A dermoscopic image of a skin lesion: 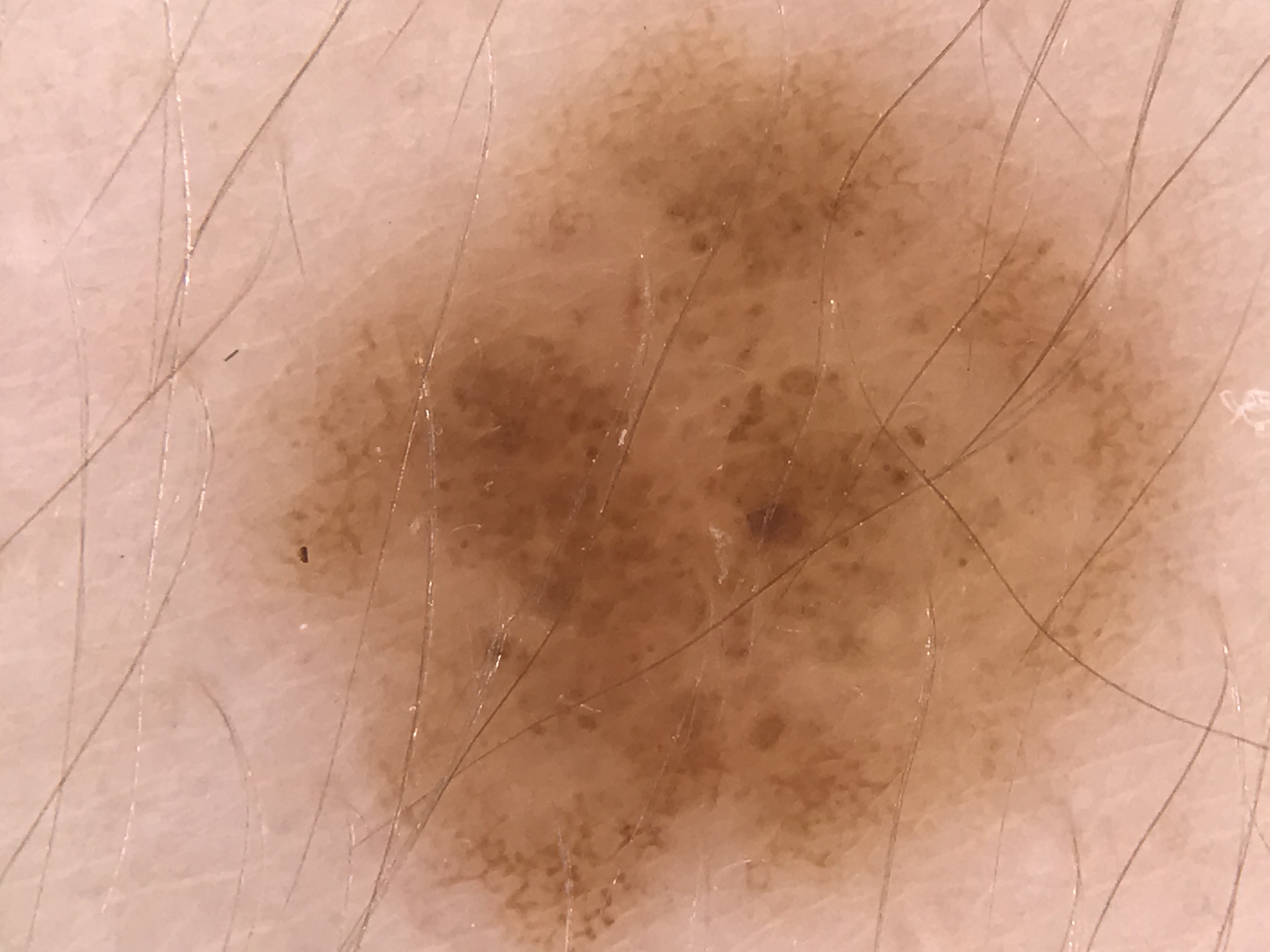label: dysplastic compound nevus (expert consensus).